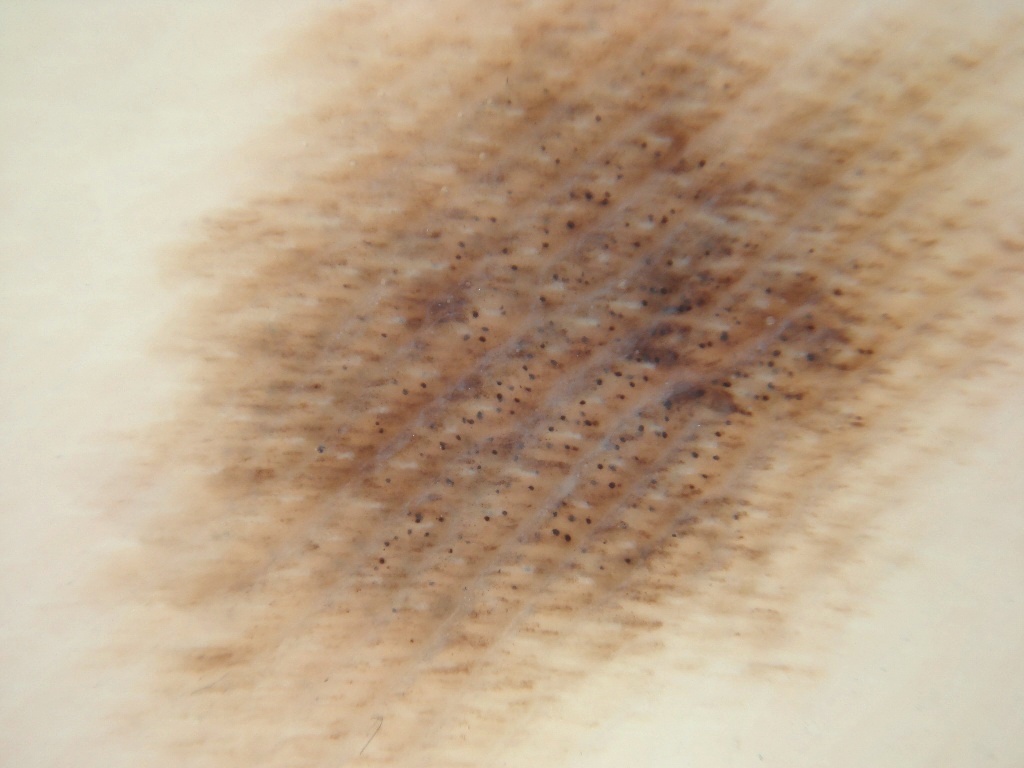  image:
    modality: dermoscopy
  lesion_location: spans the dermoscopic field
  diagnosis:
    malignancy: benign
    provenance: clinical